A male patient aged 28-32 · a dermoscopy image of a single skin lesion:
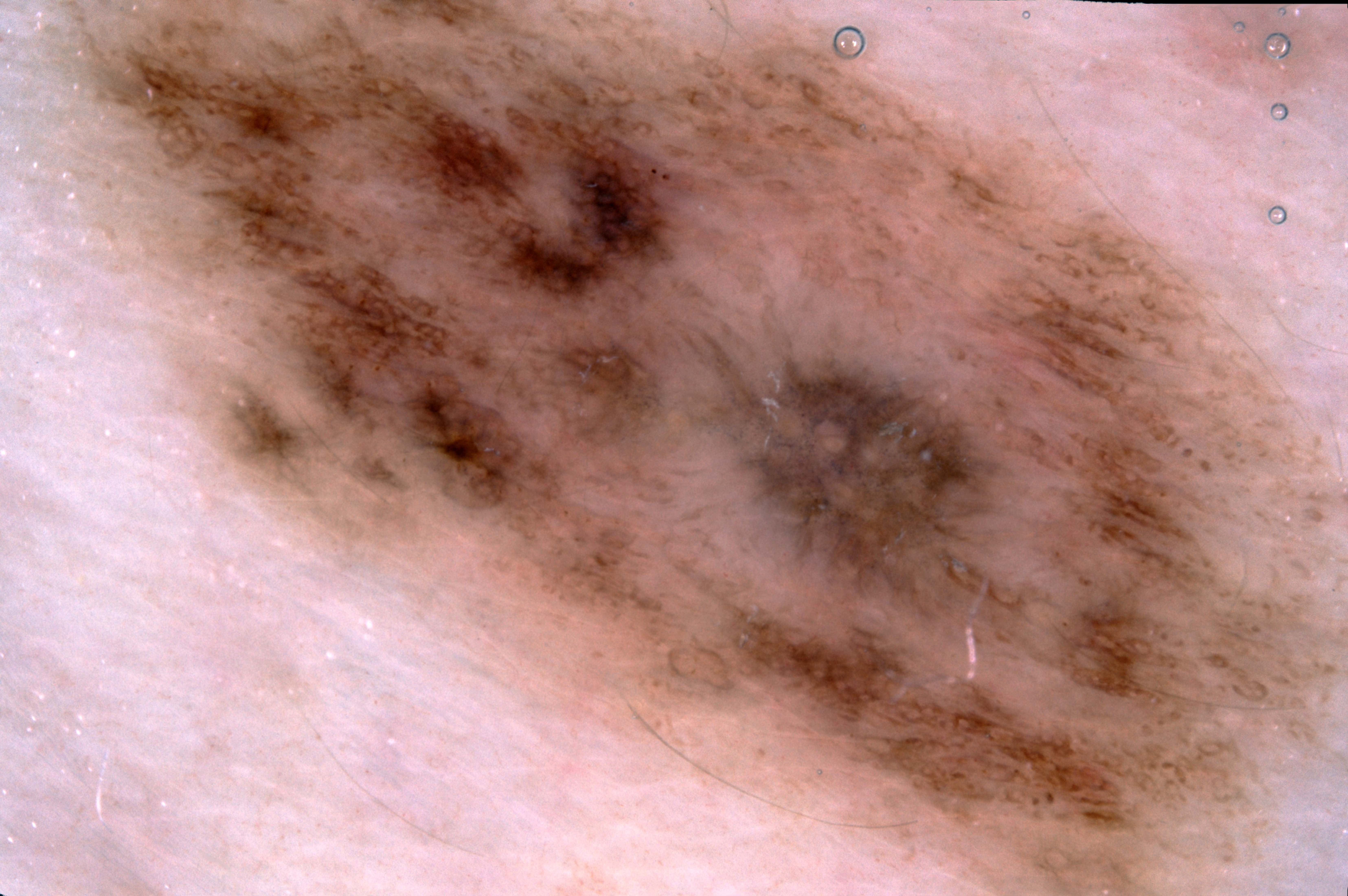The dermoscopic pattern shows pigment network. The lesion extends across the full dermoscopic field. Diagnosed as a melanocytic nevus.